A close-up photograph; symptoms reported: bleeding; the condition has been present for one to four weeks; the patient also reports fatigue; located on the back of the hand, arm, head or neck and leg; texture is reported as flat; the contributor is a male aged 40–49:
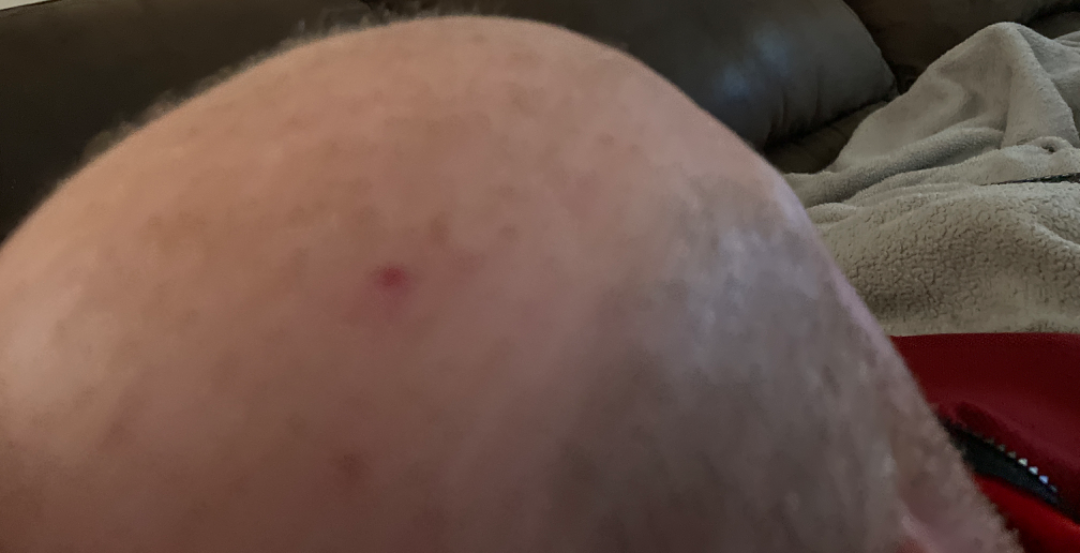assessment: indeterminate from the photograph.